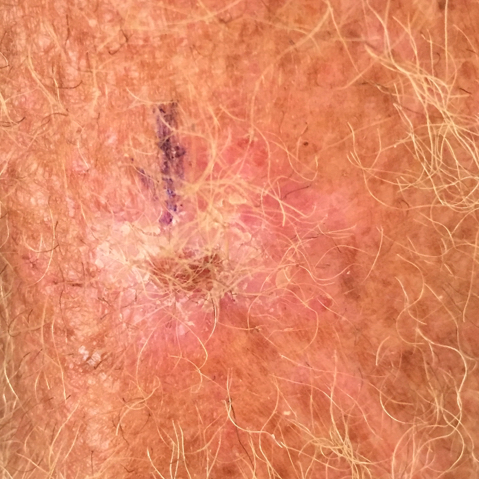| field | value |
|---|---|
| Fitzpatrick | II |
| modality | clinical photo |
| exposure history | alcohol use, pesticide exposure |
| patient | male, age 62 |
| symptoms | itching, change in appearance, bleeding, elevation, growth |
| impression | actinic keratosis (clinical consensus) |